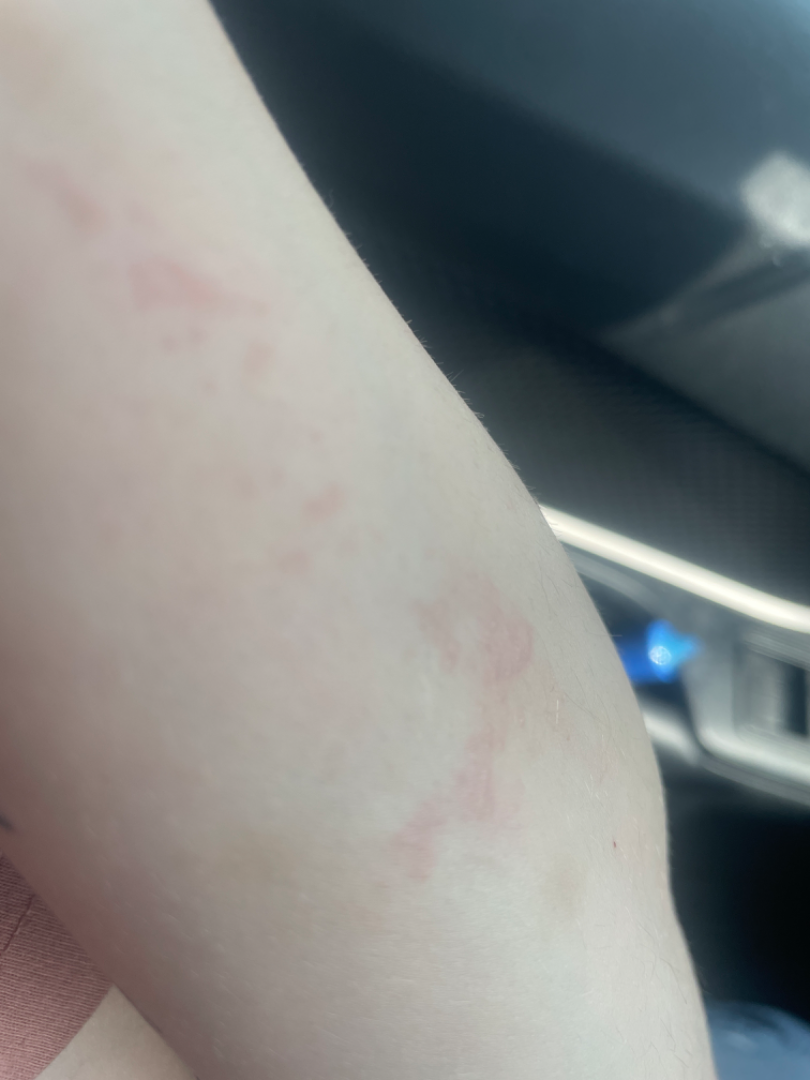The skin findings could not be characterized from the image.